A dermatoscopic image of a skin lesion: 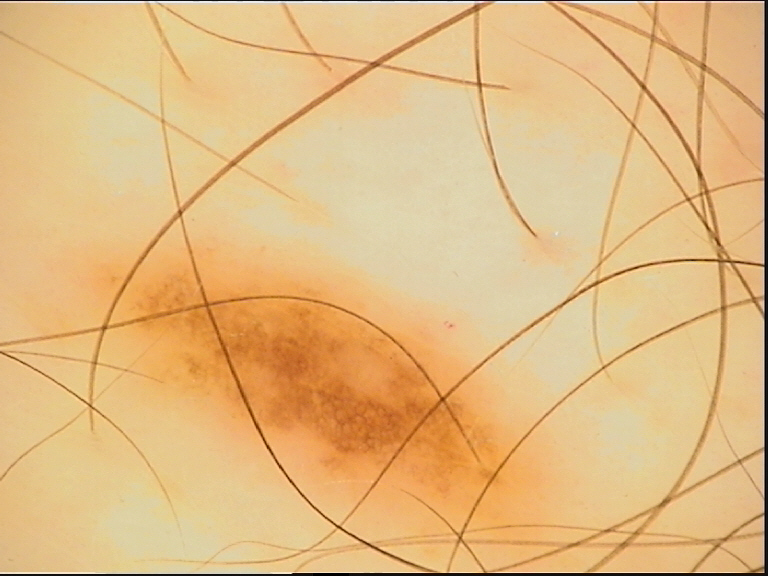Conclusion:
Diagnosed as a benign lesion — a dysplastic junctional nevus.